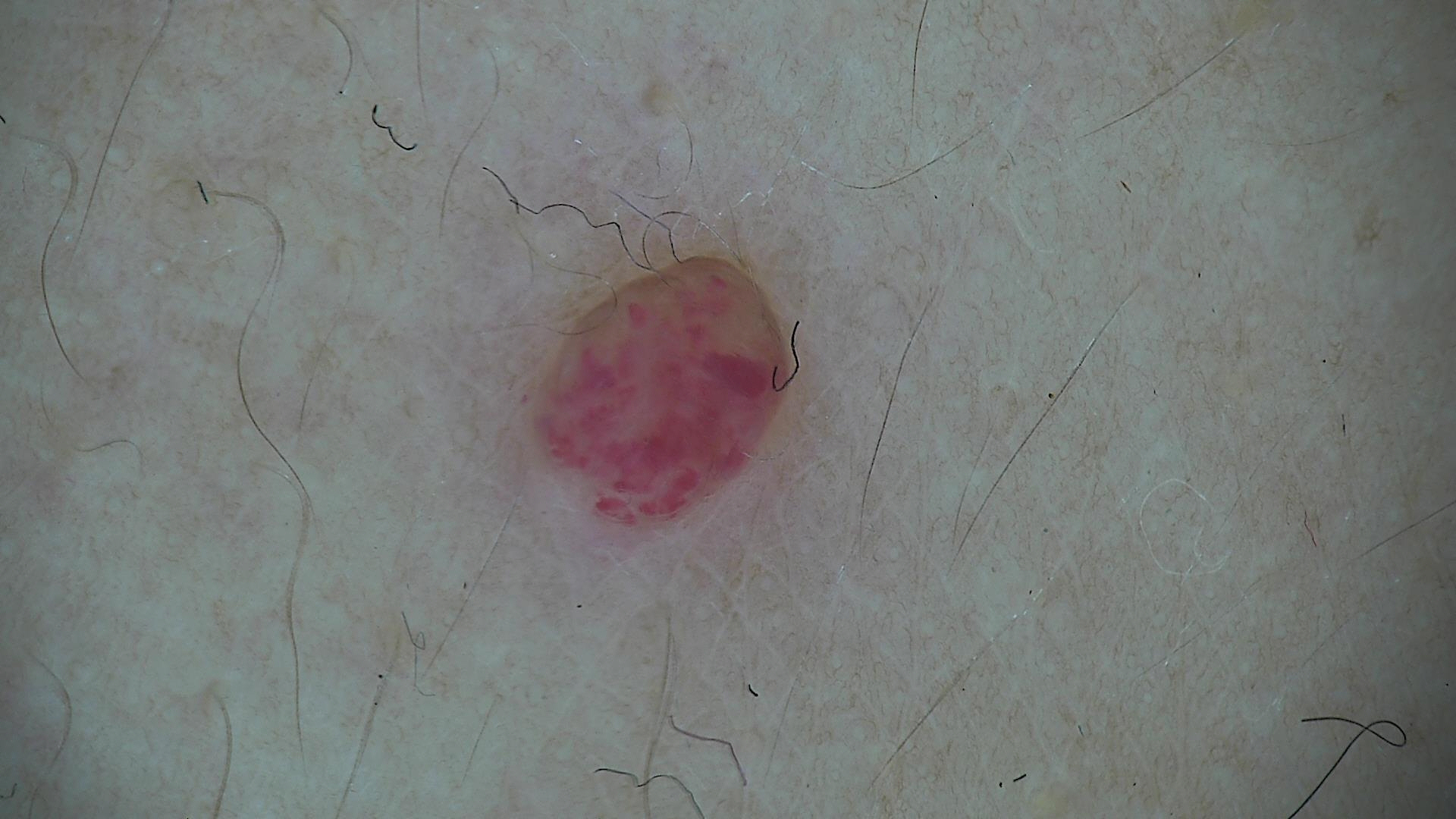image type: dermoscopy
classification: vascular
class: hemangioma (expert consensus)